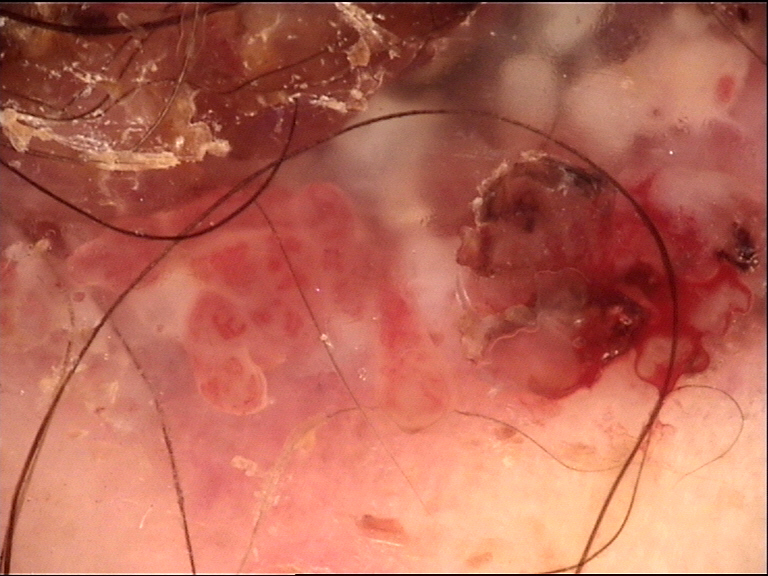A dermoscopy image of a single skin lesion. Biopsy-confirmed as a skin cancer — a squamous cell carcinoma.